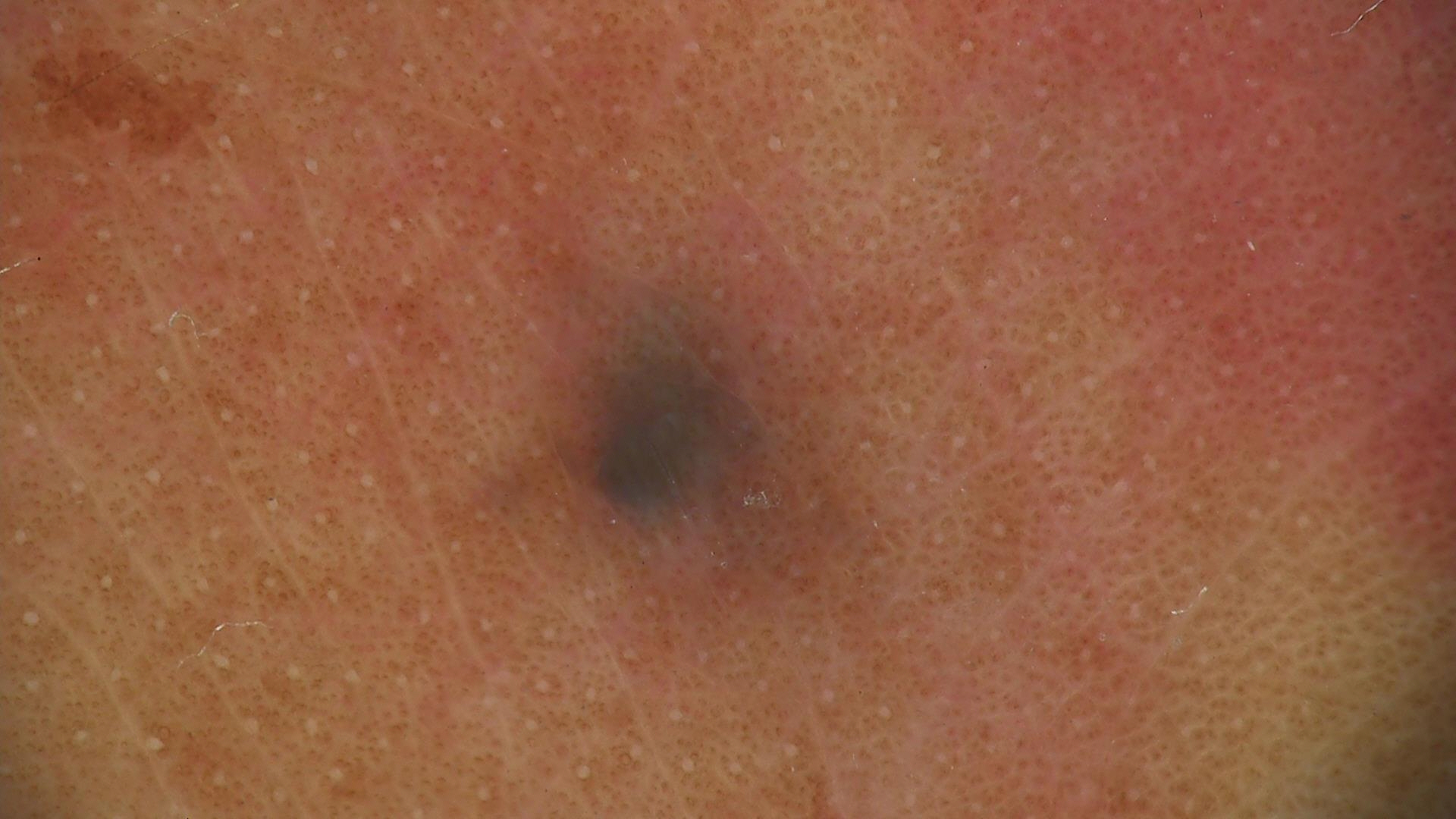image type: dermatoscopy; assessment: blue nevus (expert consensus).